Associated systemic symptoms include joint pain, fatigue and chills · skin tone: non-clinician graders estimated MST 2–3 · a close-up photograph · the patient notes the condition has been present for one to four weeks · the lesion involves the back of the hand, back of the torso, leg and arm · the patient notes burning, pain, itching and bleeding: 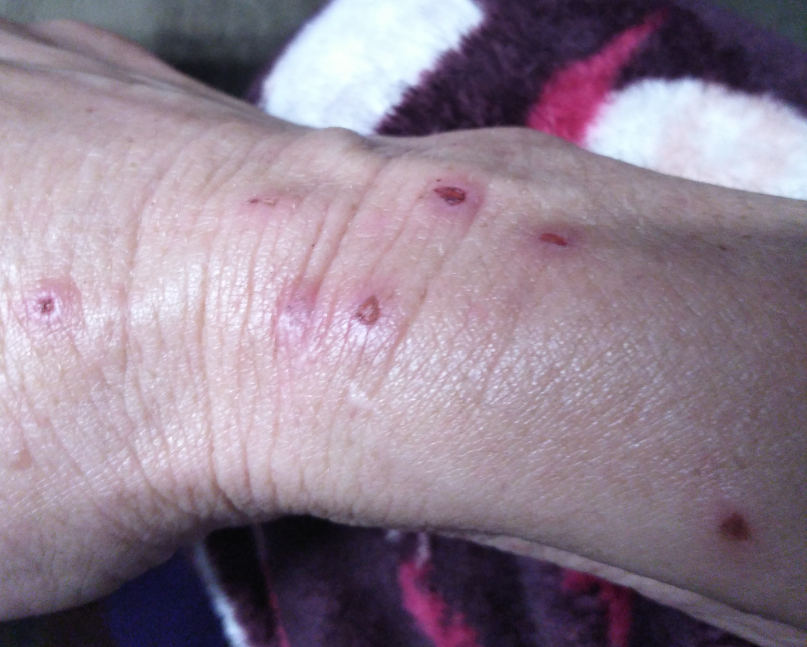Assessment: The reviewing dermatologist's impression was: most consistent with Prurigo nodularis.